This is a close-up image; the front of the torso is involved.
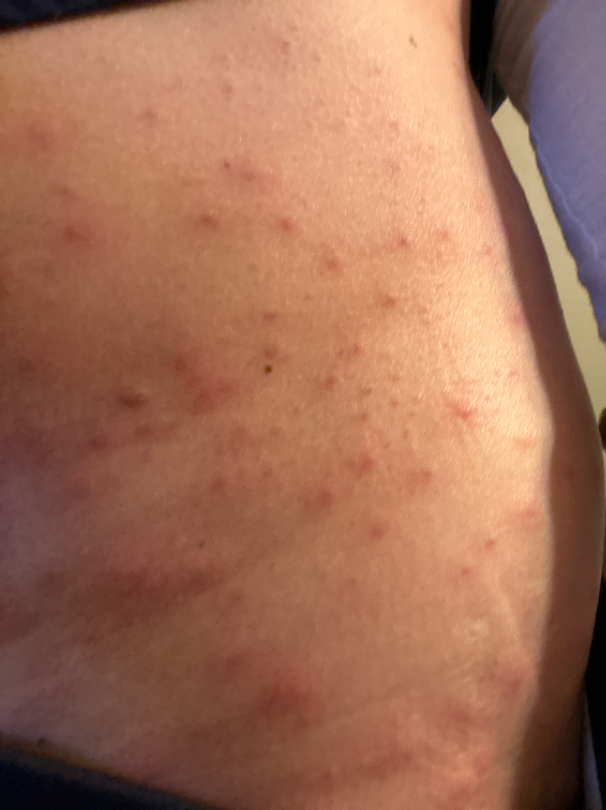Q: What is the differential diagnosis?
A: Scabies, Folliculitis and Insect Bite were each considered, in no particular order